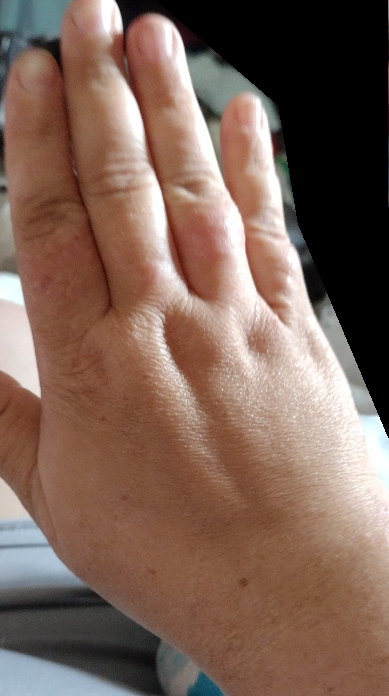No differential diagnosis could be assigned on photographic review.
An image taken at a distance.
The lesion is described as raised or bumpy and fluid-filled.
The arm, back of the hand and leg are involved.
Reported duration is less than one week.
The patient described the issue as a rash.
Skin tone: self-reported FST IV.
The patient is 30–39, female.